A male patient about 75 years old, a dermoscopic image of a skin lesion:
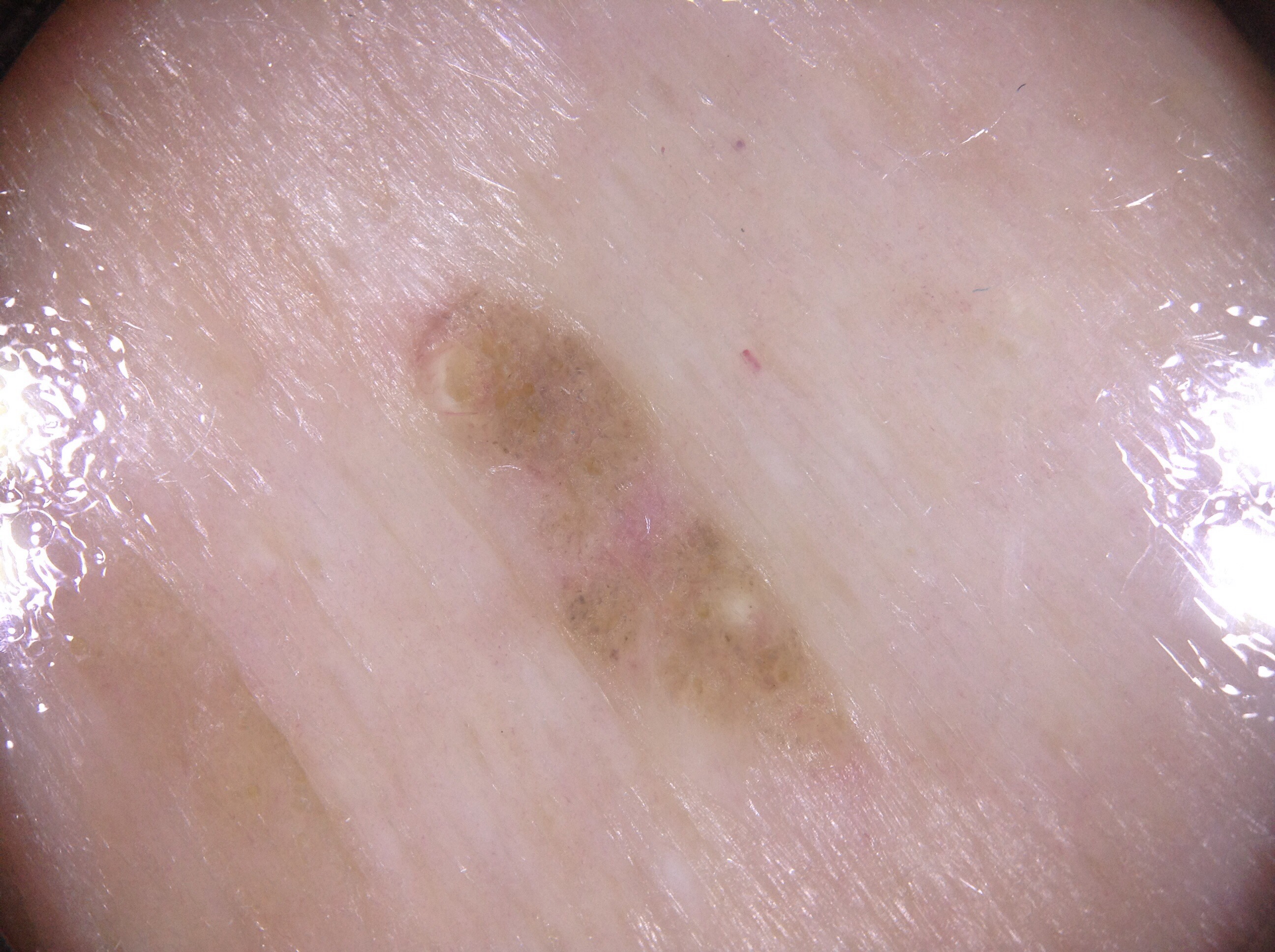Findings: The lesion occupies roughly 6% of the field. Dermoscopically, the lesion shows milia-like cysts; no pigment network, negative network, or streaks. The lesion's extent is 428/297/817/714. Impression: The lesion was assessed as a seborrheic keratosis, a benign lesion.